The patient describes having few moles overall · a female subject aged 68 · the patient says their skin tans without first burning · imaged for a research study, with no referral diagnosis recorded:
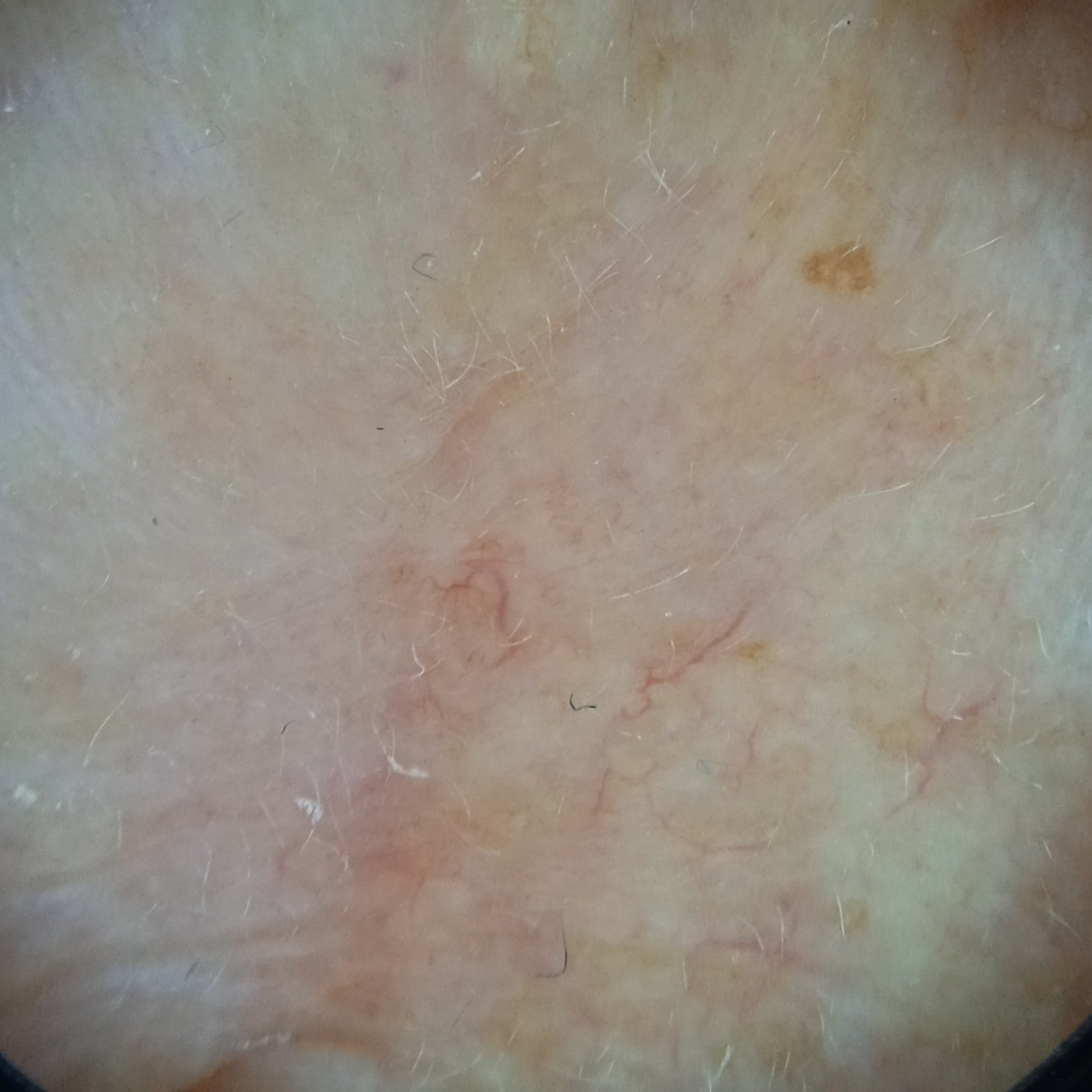location = the face; lesion size = 8.2 mm; assessment = basal cell carcinoma (dermatologist consensus).